Symptoms reported: bothersome appearance and itching. Self-categorized by the patient as a rash. Present for one to four weeks. This is a close-up image. The patient is 18–29, female. The affected area is the leg. The lesion is described as fluid-filled and raised or bumpy:
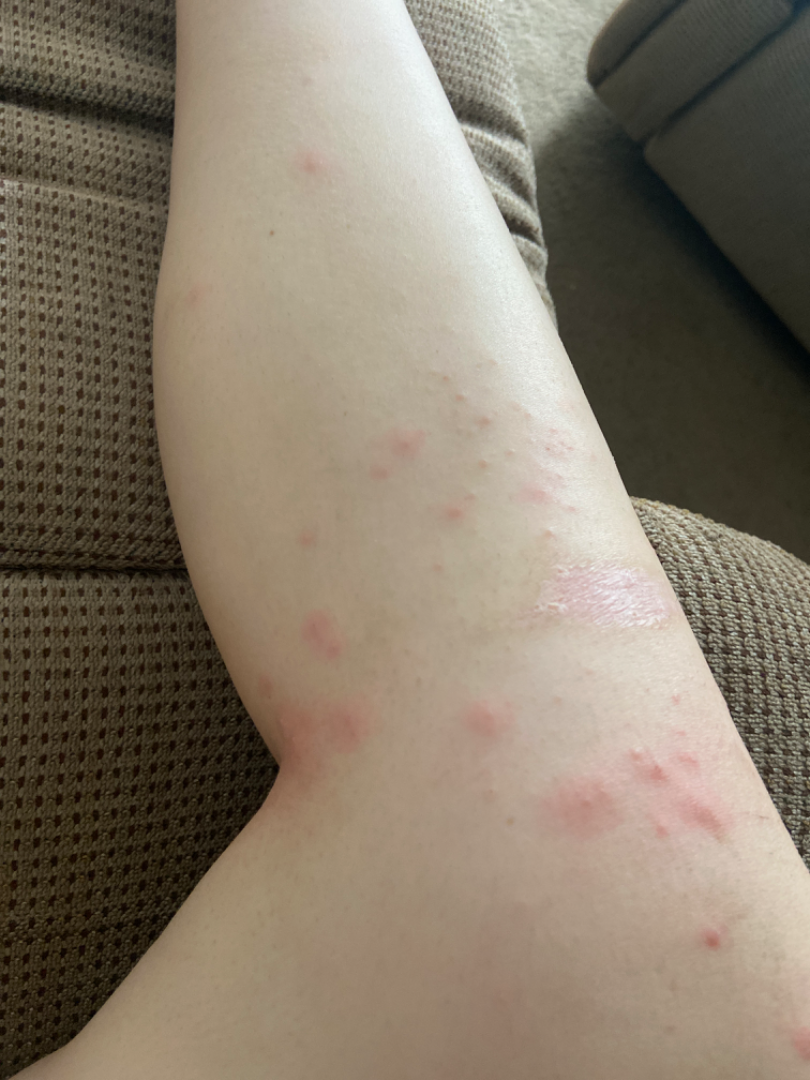Findings:
Folliculitis (weight 1.00).